Female contributor, age 60–69. This image was taken at an angle. The affected area is the arm:
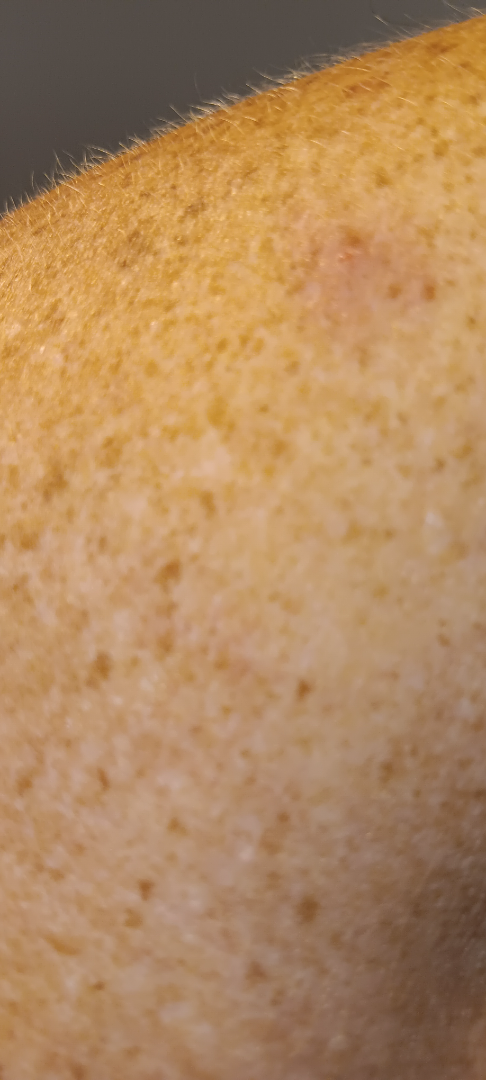assessment: could not be assessed.